A dermoscopic photograph of a skin lesion.
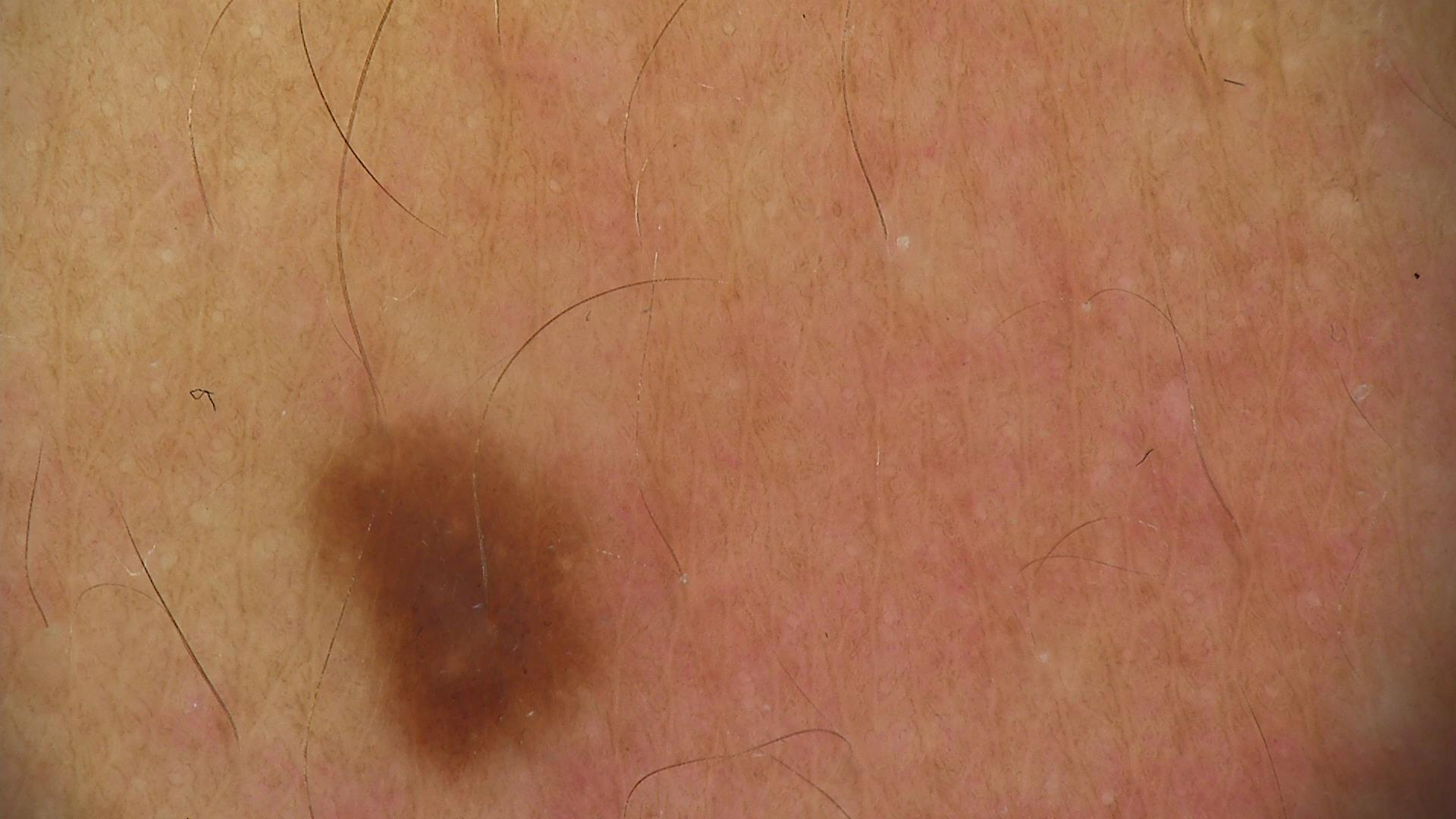diagnosis = junctional nevus (expert consensus).